An image taken at an angle: 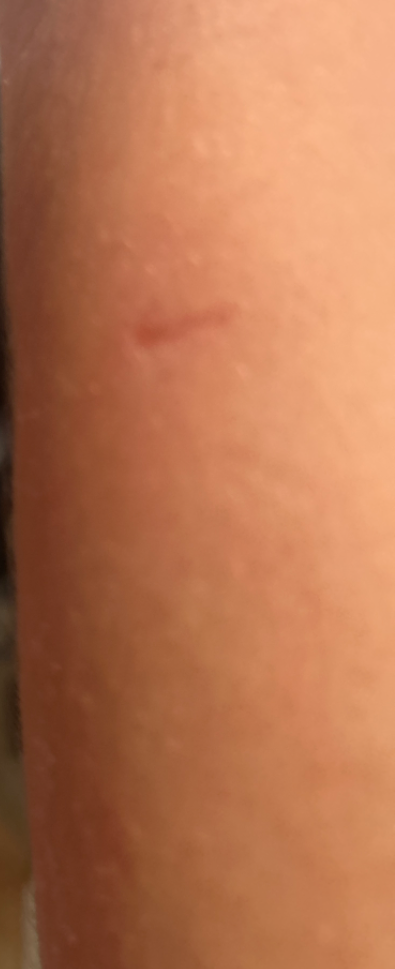The skin findings could not be characterized from the image.